The photograph was taken at an angle · the condition has been present for one to three months · located on the top or side of the foot · the patient indicates the lesion is raised or bumpy and rough or flaky · male contributor, age 70–79 · the patient indicates bleeding, itching, bothersome appearance and burning · self-categorized by the patient as a rash: 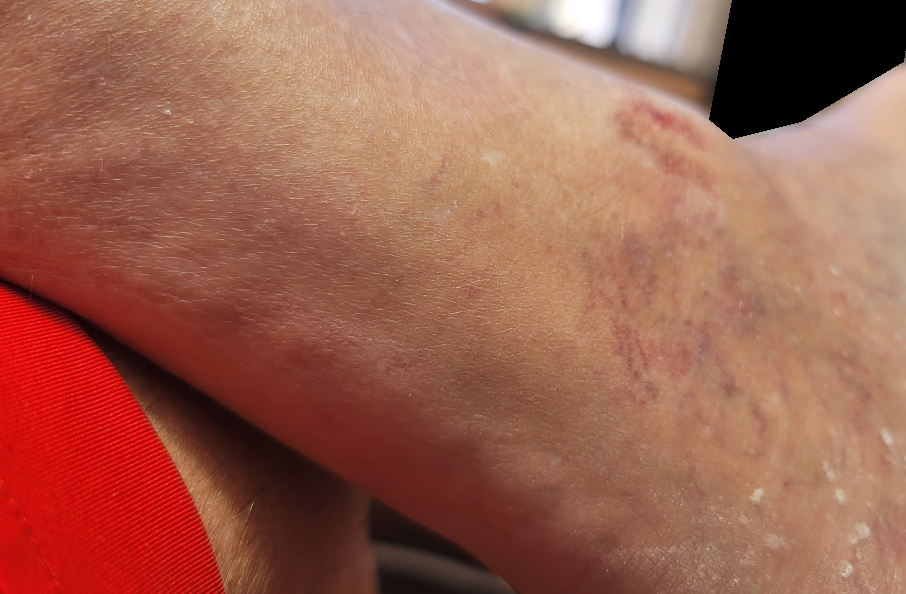Findings:
• impression — Stasis Dermatitis (40%); Tinea (40%); Eczema (20%)